A clinical photo of a skin lesion taken with a smartphone; the patient was assessed as Fitzpatrick skin type II; the chart notes alcohol use and pesticide exposure: 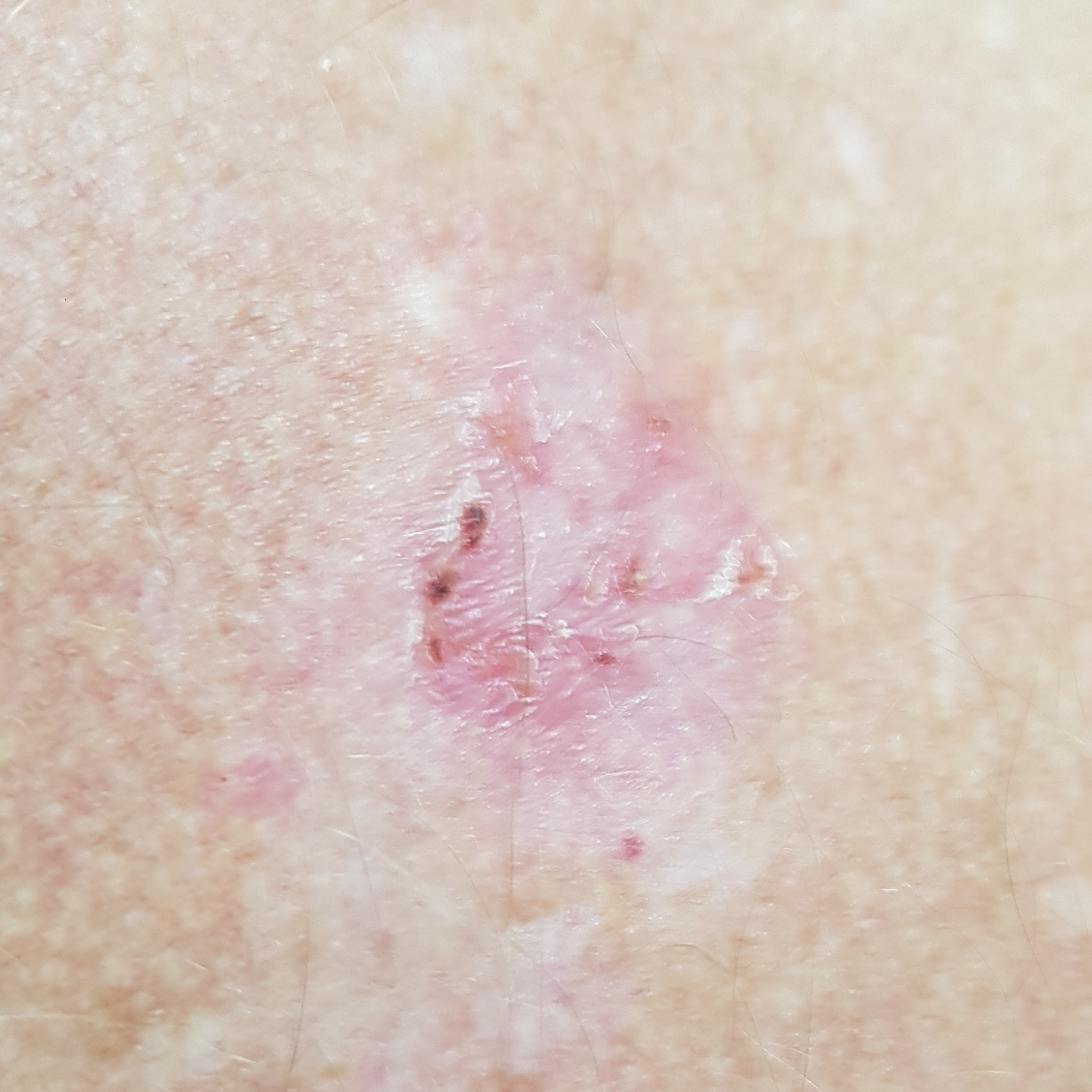* region — the back
* pathology — basal cell carcinoma (biopsy-proven)